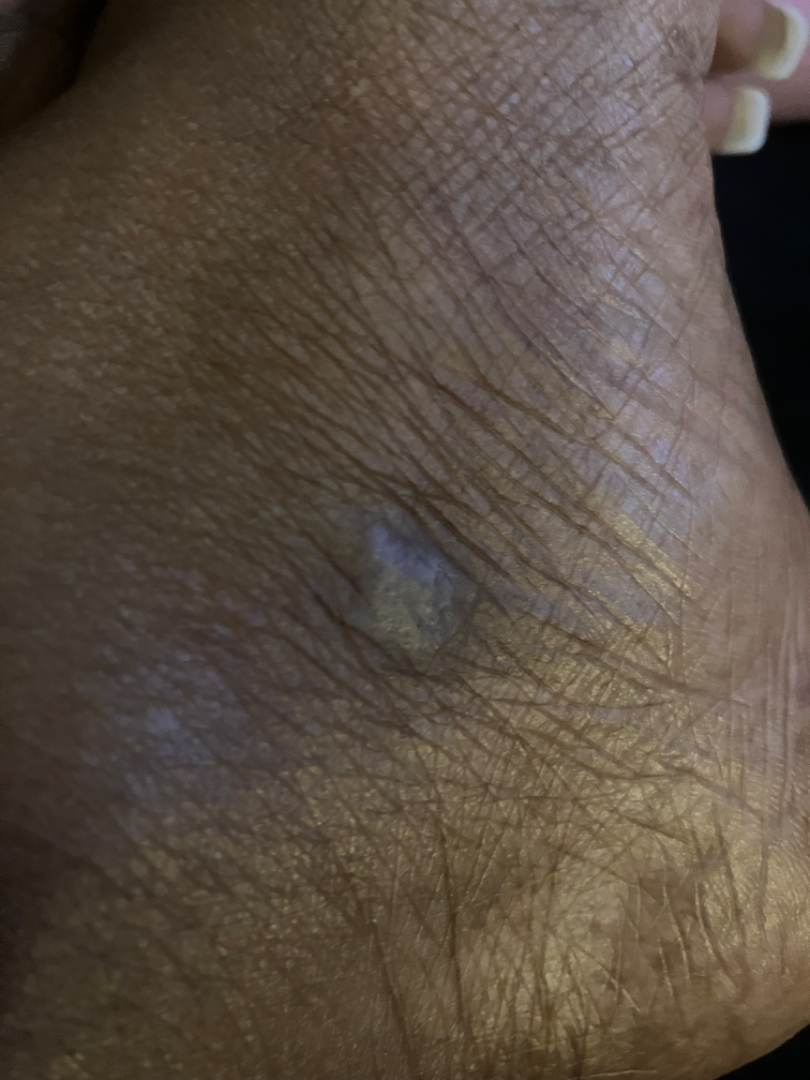Impression: On photographic review, Keratosis (considered); Verruca vulgaris (considered); Lichen Simplex Chronicus (considered).